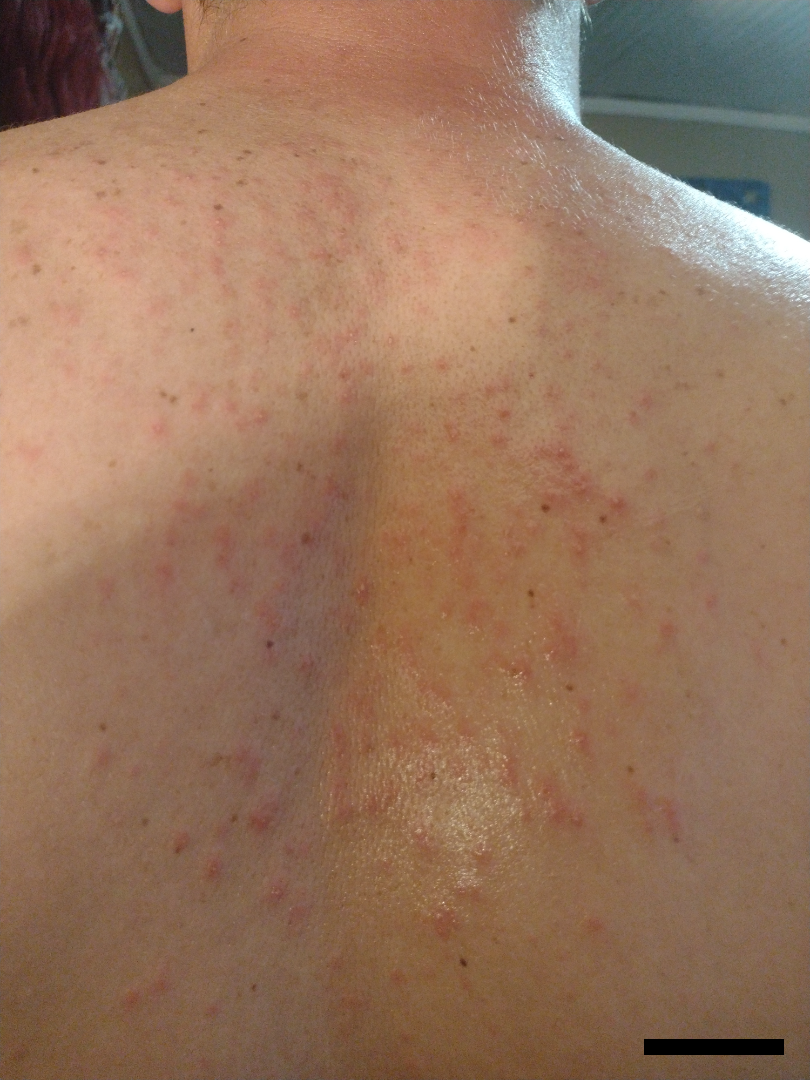History: The patient indicates associated fatigue and joint pain. The patient indicates the condition has been present for about one day. The lesion is described as fluid-filled and raised or bumpy. The patient described the issue as a rash. Located on the back of the torso, front of the torso and head or neck. A close-up photograph. The lesion is associated with darkening, enlargement and bothersome appearance. Impression: On photographic review, Folliculitis (67%); Miliaria (33%).